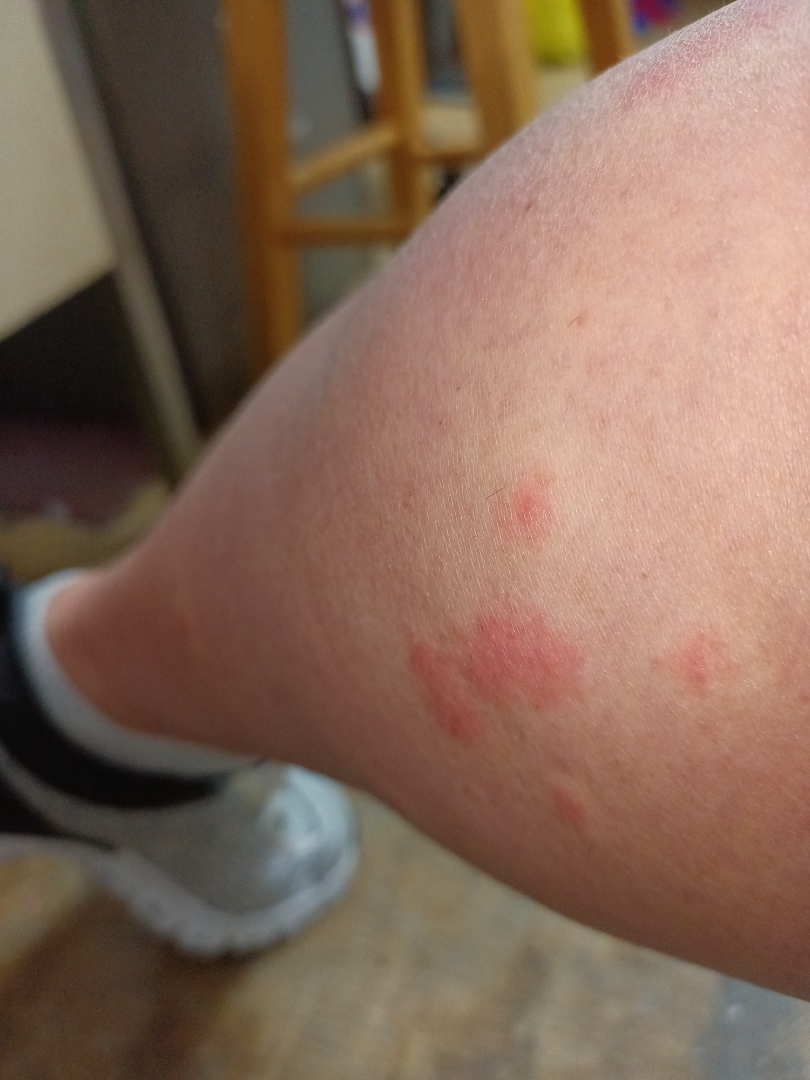The skin condition could not be confidently assessed from this image. The lesion is described as raised or bumpy. The lesion involves the leg. The patient considered this a rash. The contributor notes the condition has been present for less than one week. The photograph is a close-up of the affected area. The lesion is associated with itching.